Acquired for a research image collection, with no referral diagnosis; a male patient 73 years of age; a dermoscopic image of a skin lesion; the patient describes having numerous moles; the patient says their skin reddens with sun exposure; the patient reports a personal history of cancer — 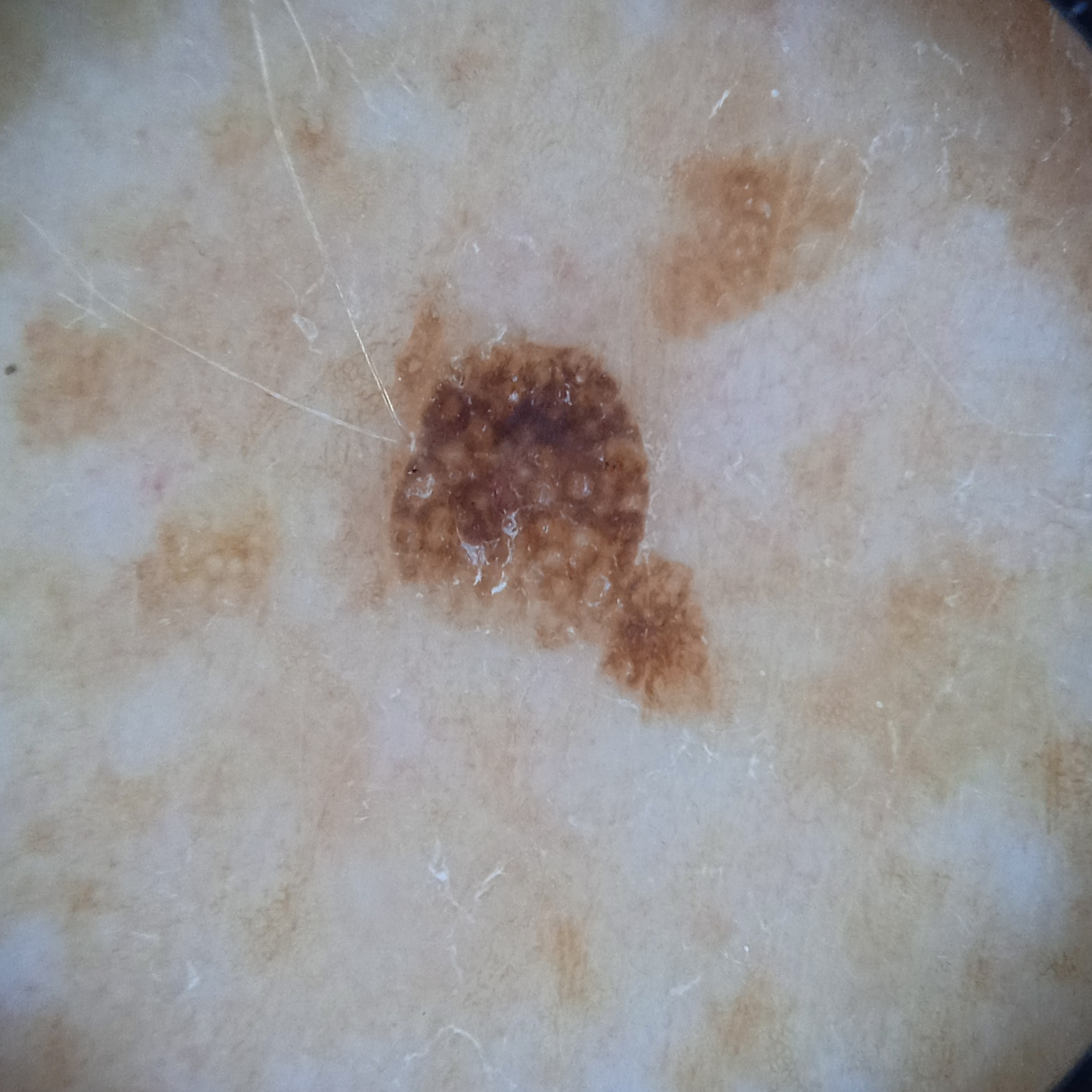lesion_location: the back
lesion_size:
  diameter_mm: 5.5
diagnosis:
  name: seborrheic keratosis
  malignancy: benign
  unanimous: true